Imaged for a research study, with no referral diagnosis recorded · the patient says their skin reddens painfully with sun exposure · a dermoscopic image of a skin lesion · a moderate number of moles by the patient's own estimate: 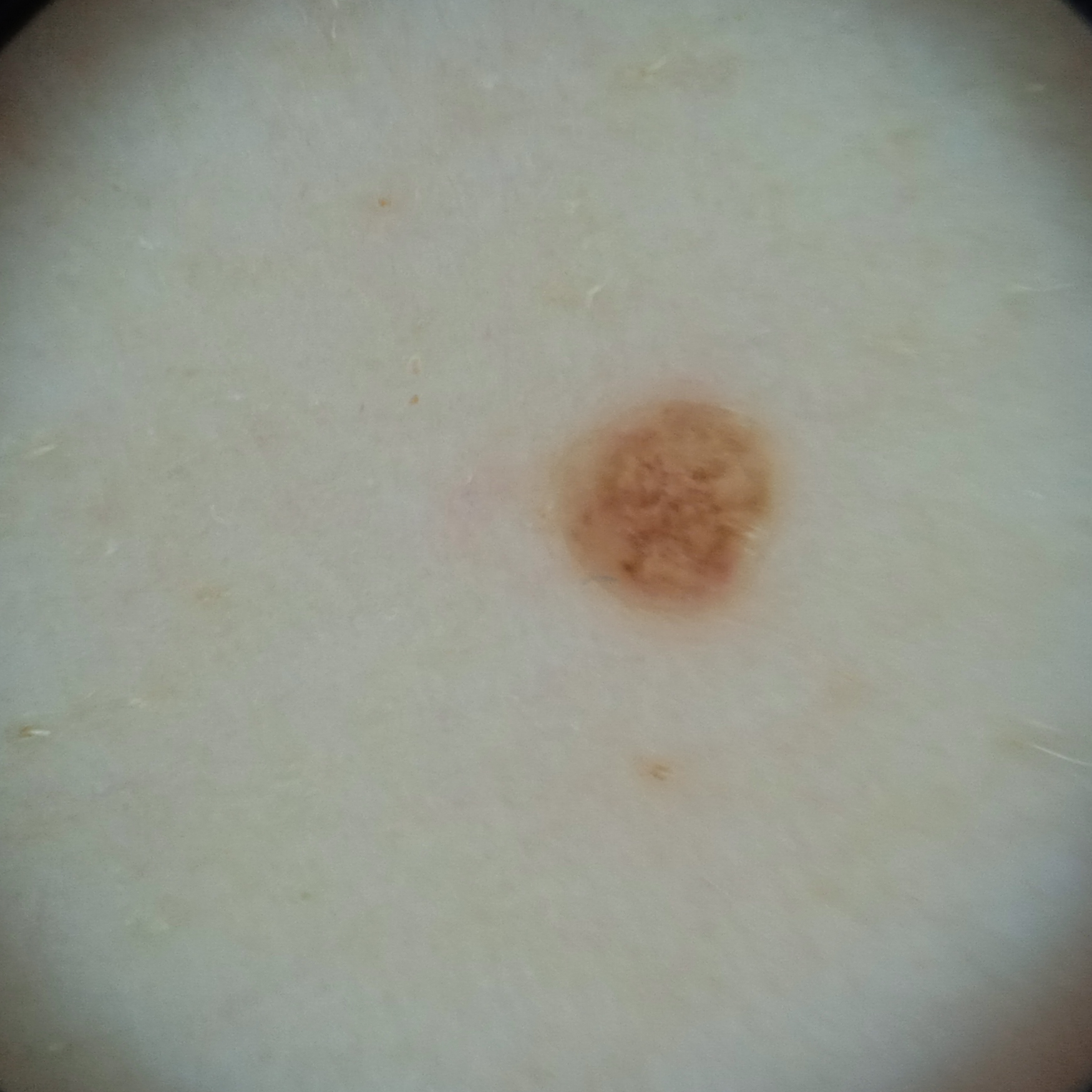The lesion is about 2.2 mm across. The lesion was assessed as a melanocytic nevus.